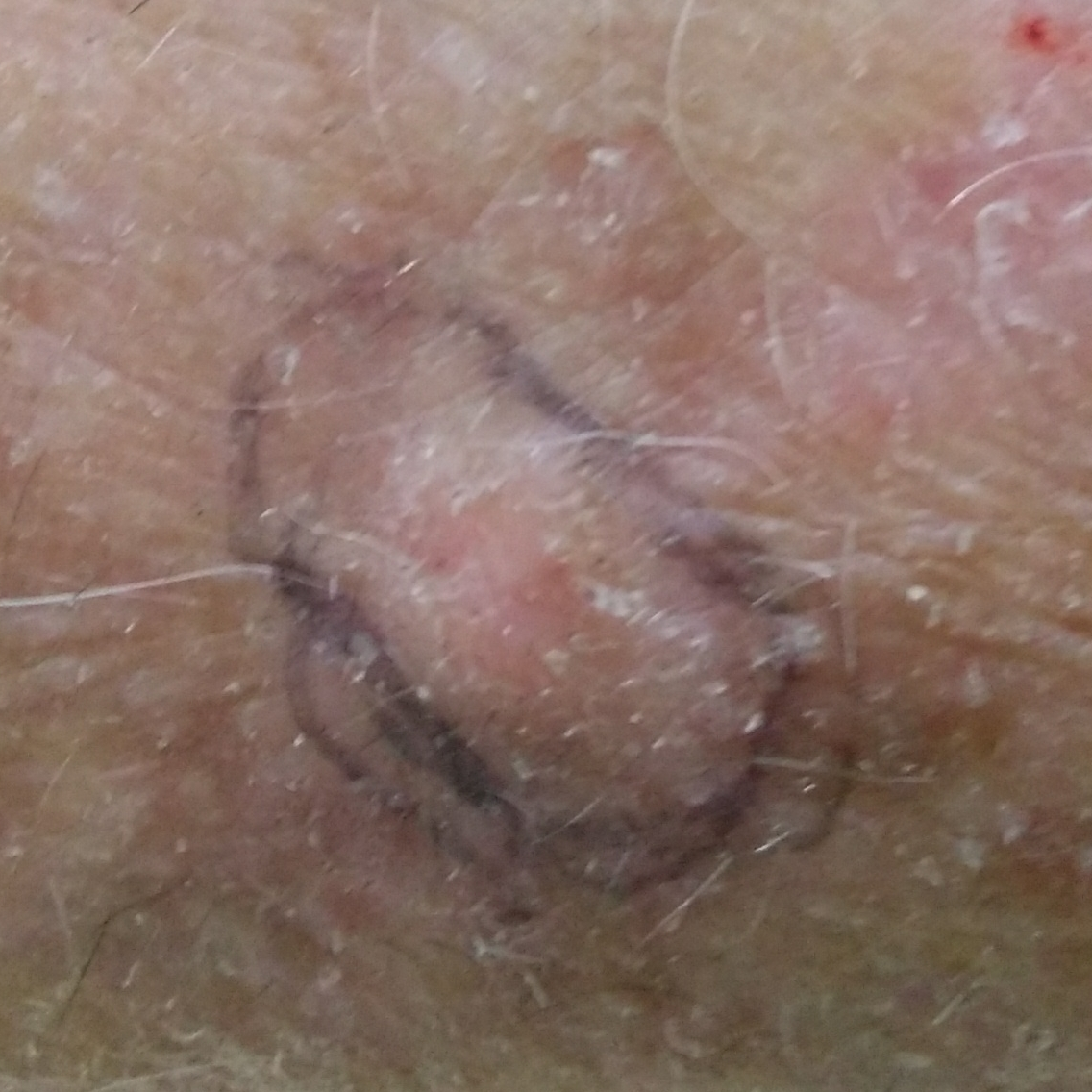• exposure history — no alcohol use, no prior skin cancer (patient or family)
• Fitzpatrick — II
• imaging — clinical photograph
• subject — male, in their early 80s
• location — a forearm
• diameter — approx. 7 × 7 mm
• symptoms — itching
• diagnosis — actinic keratosis (biopsy-proven)